A dermoscopic image of a skin lesion · a female patient in their mid-80s or older — 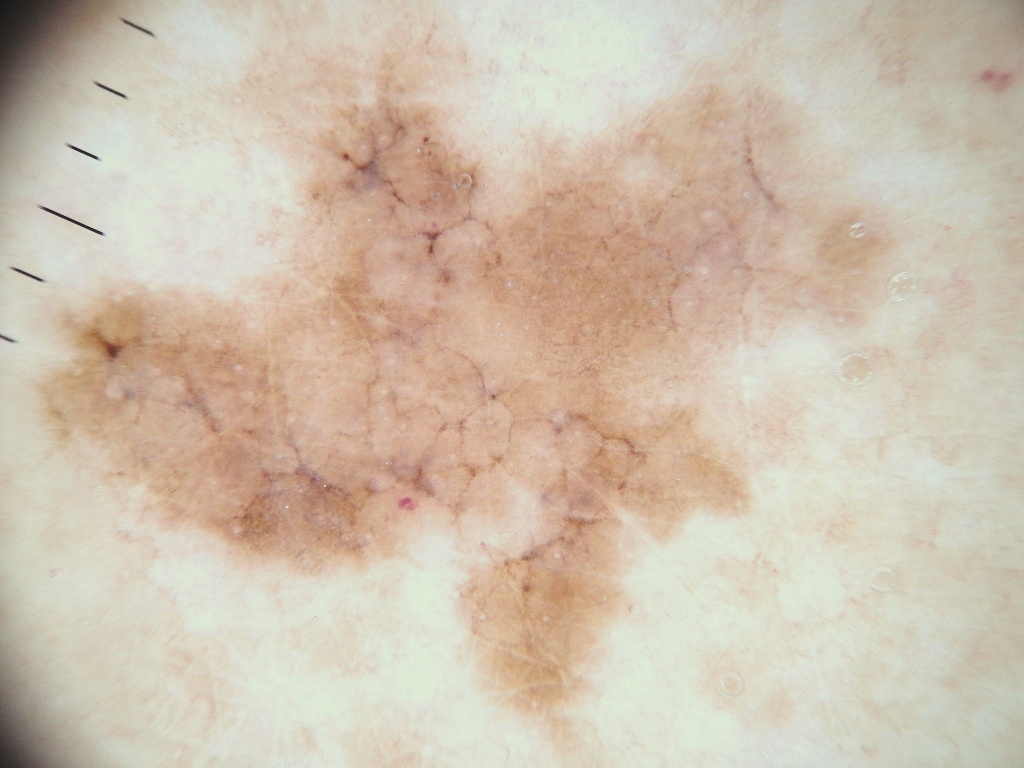frame_clip: lesion extends past the field edge
lesion_location:
  bbox_xyxy:
    - 20
    - 0
    - 929
    - 764
dermoscopic_features:
  present: []
  absent:
    - pigment network
    - streaks
    - negative network
    - milia-like cysts
    - globules
diagnosis:
  name: melanoma
  malignancy: malignant
  lineage: melanocytic
  provenance: histopathology